Fitzpatrick skin type II. By history, no prior malignancy (patient or family) and no alcohol use. A clinical photograph of a skin lesion. A female patient in their early 70s: 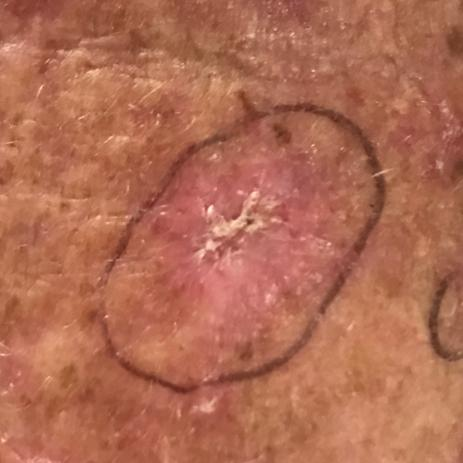location: a forearm, diagnostic label: actinic keratosis (clinical consensus).